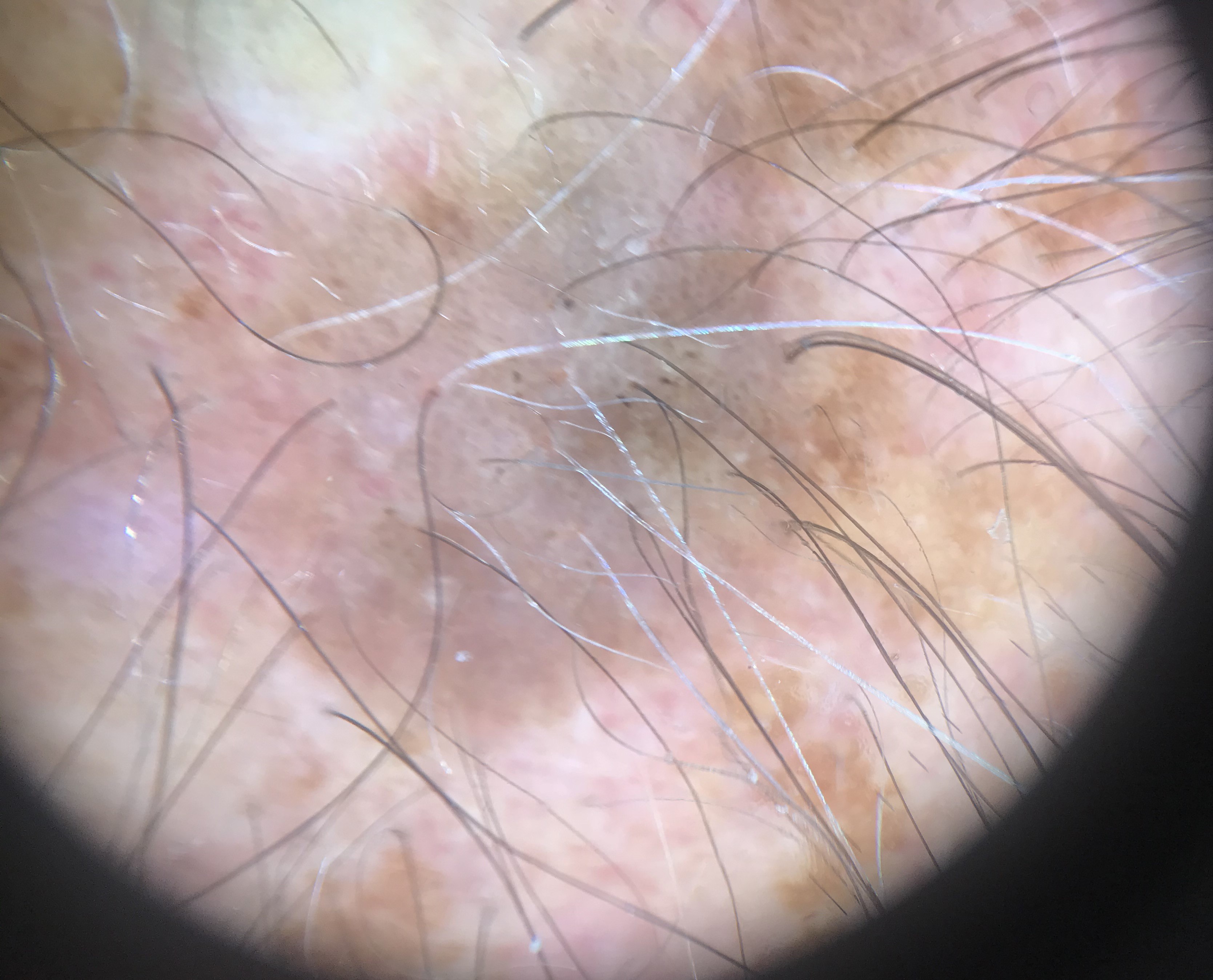Conclusion:
Diagnosed as a seborrheic keratosis.